A dermoscopic photograph of a skin lesion: 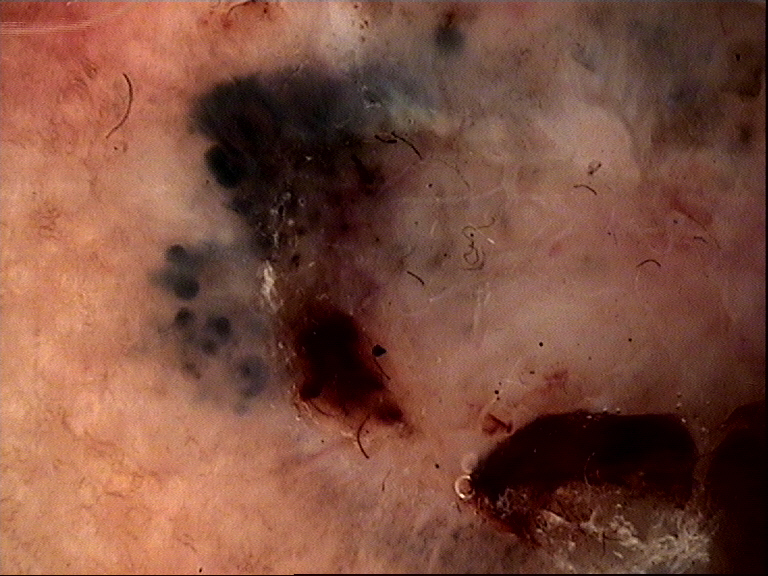pathology: basal cell carcinoma (biopsy-proven)